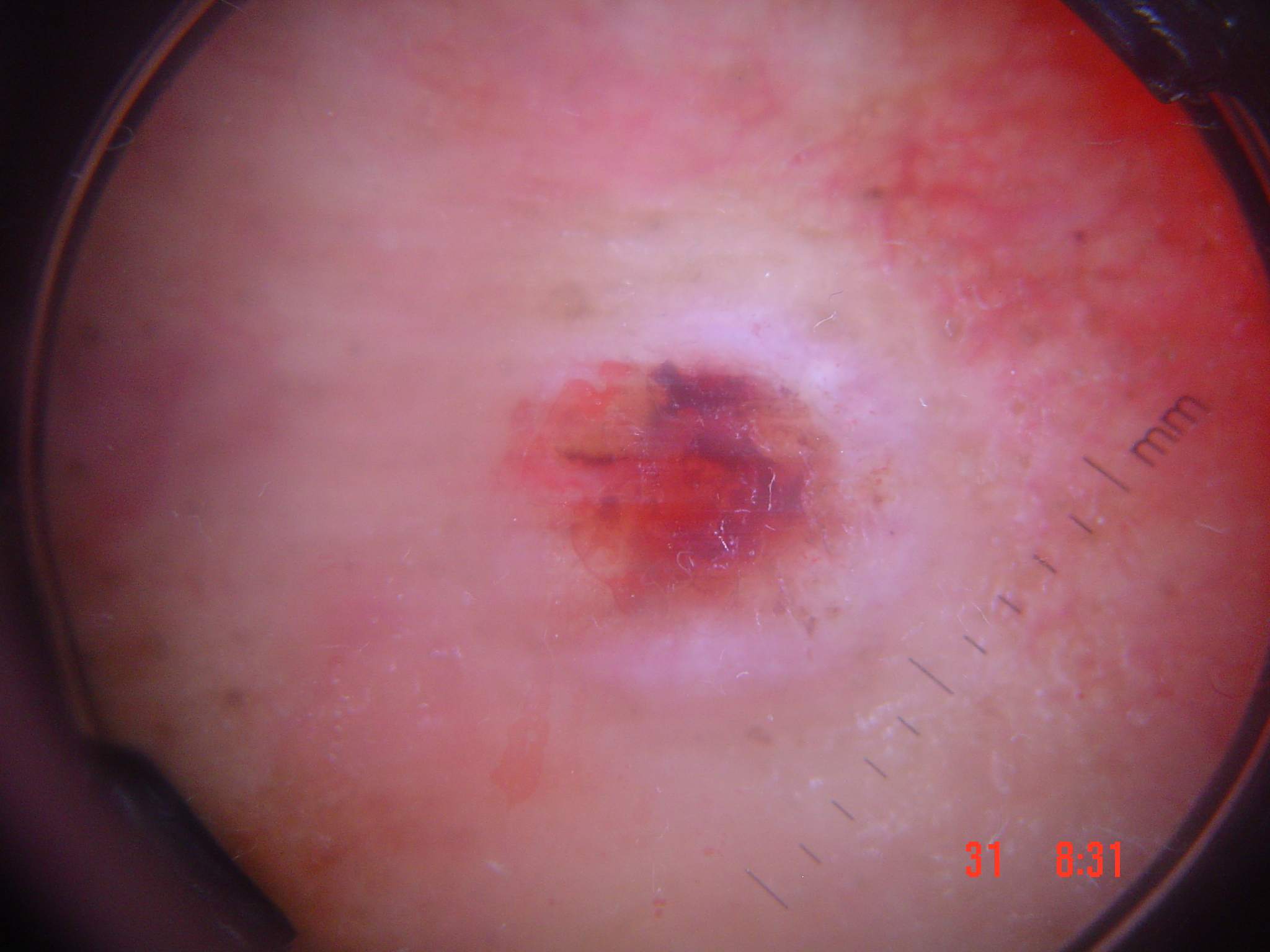subtype = keratinocytic
label = squamous cell carcinoma (biopsy-proven)